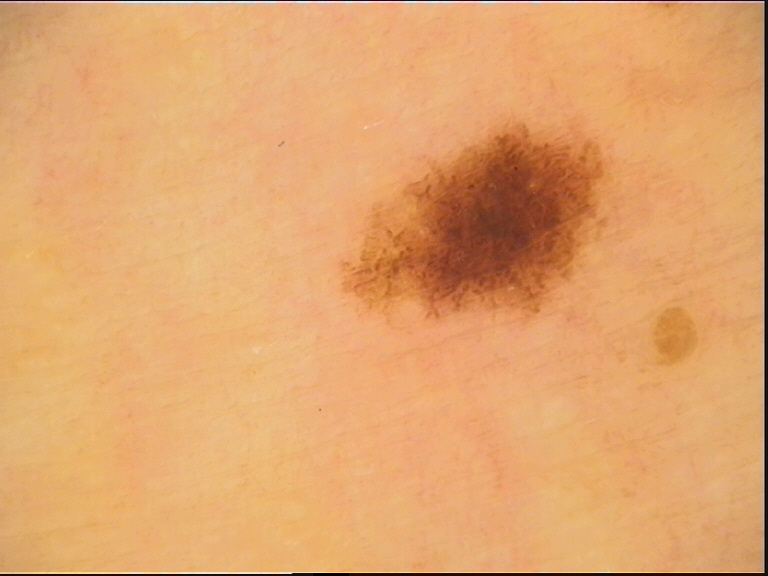A dermoscopic image of a skin lesion. Consistent with a benign lesion — a dysplastic junctional nevus.